The patient is FST I; a skin lesion imaged with contact-polarized dermoscopy; a male subject aged 68 to 72 — 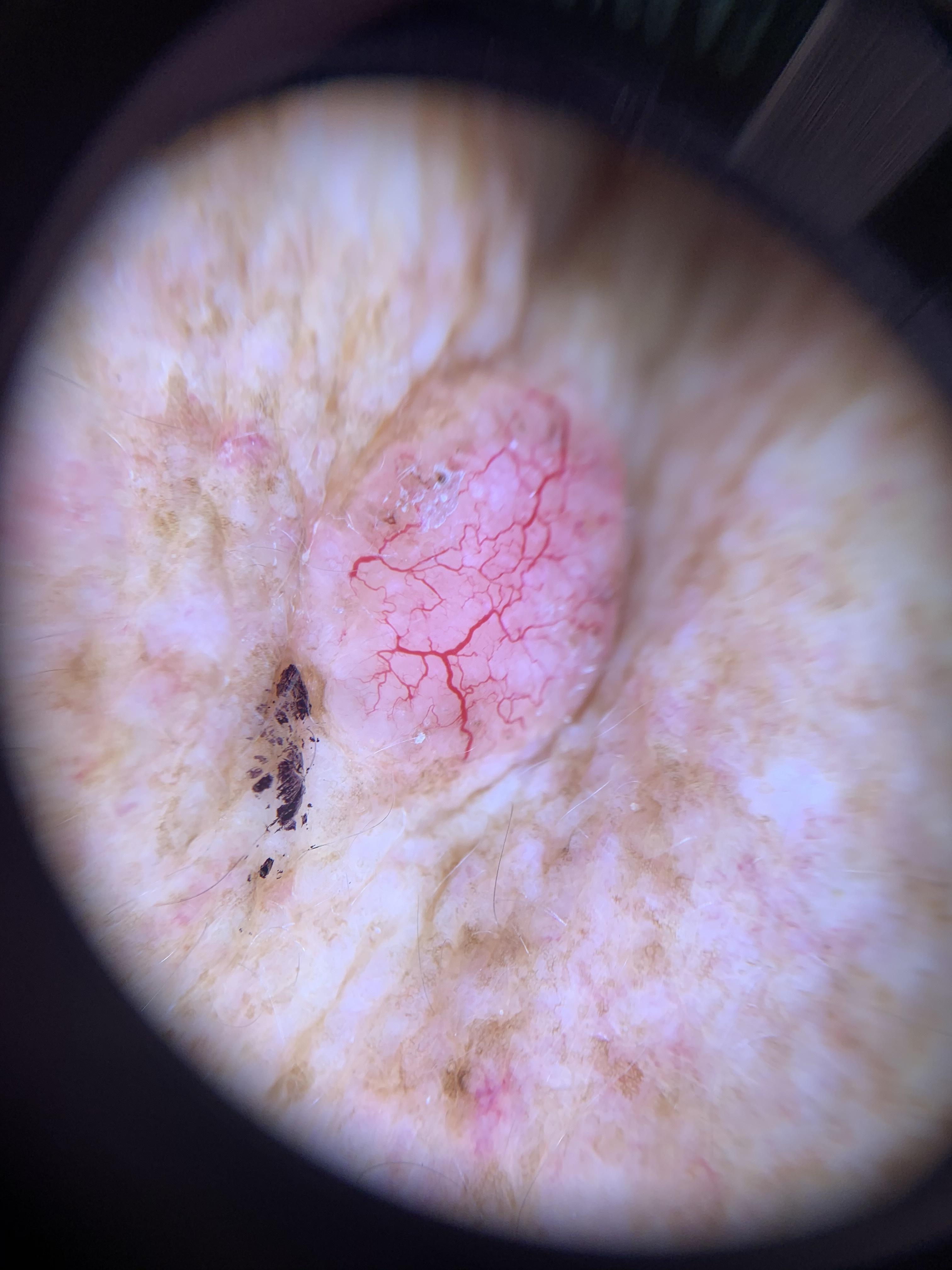The lesion was found on an upper extremity. On biopsy, the diagnosis was an adnexal lesion — a basal cell carcinoma.